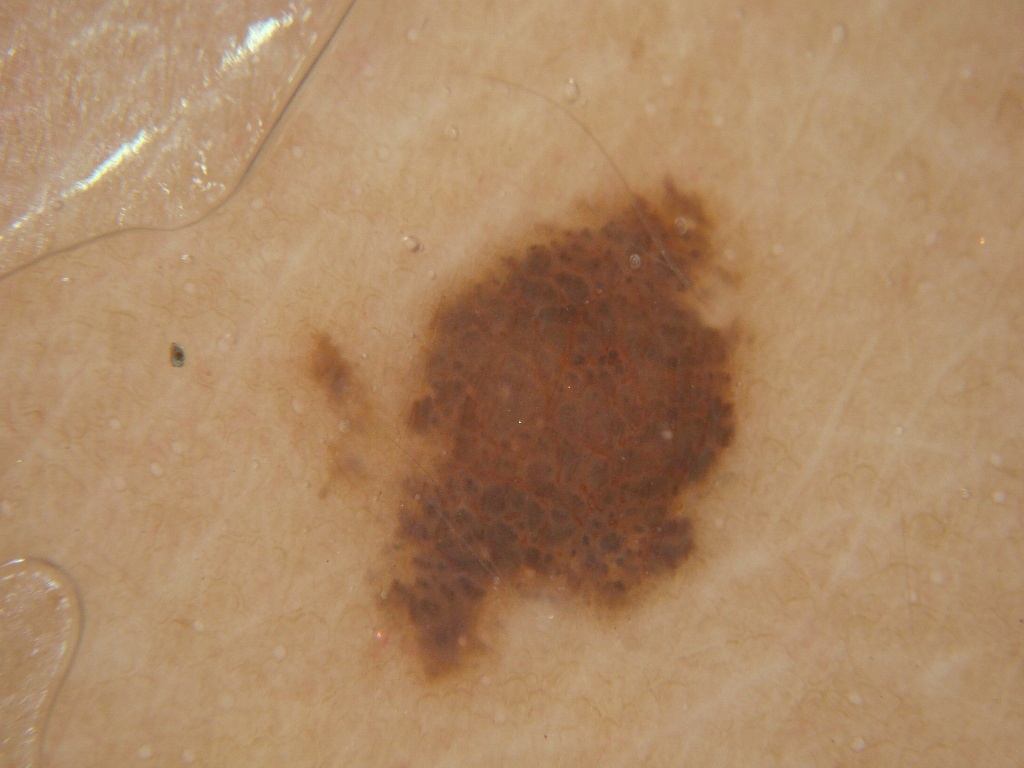Case summary:
A dermoscopic image of a skin lesion. A female patient aged 23 to 27. In (x1, y1, x2, y2) order, the lesion occupies the region [303, 176, 753, 684]. The lesion takes up a moderate portion of the field. The dermoscopic pattern shows globules.
Conclusion:
Clinically diagnosed as a melanocytic nevus, a benign skin lesion.